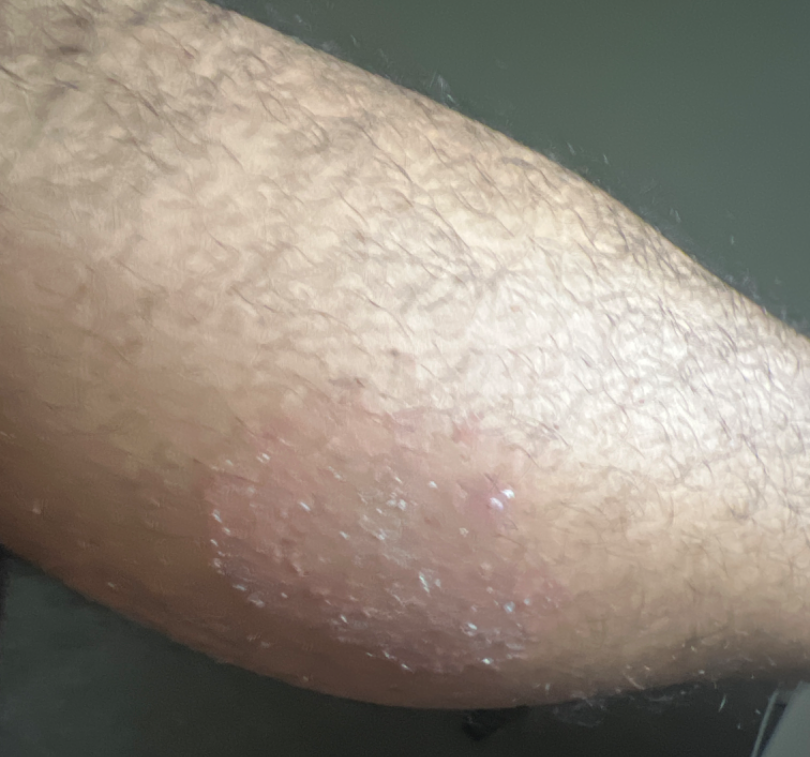{
  "duration": "one to four weeks",
  "symptoms": "itching",
  "patient": "male, age 18–29",
  "patient_category": "a rash",
  "shot_type": "at an angle",
  "body_site": "leg",
  "differential": "Tinea"
}